A clinical photograph of a skin lesion · a subject age 51:
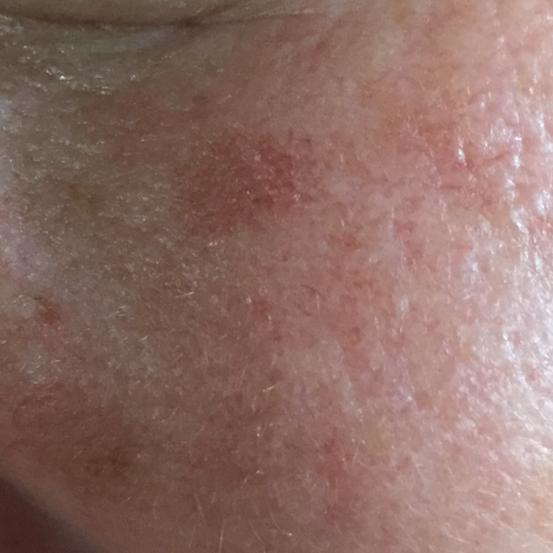The lesion was found on the face. Asymptomatic by report. Diagnosed by dermatologist consensus as an actinic keratosis.